This image was taken at a distance. The lesion involves the leg. The subject is 50–59, female: 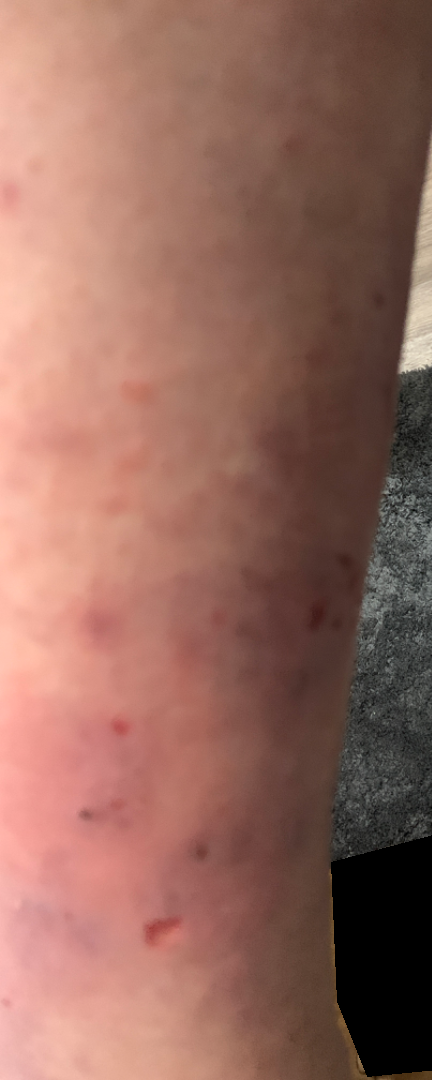Findings:
- assessment · indeterminate